The photograph is a close-up of the affected area:
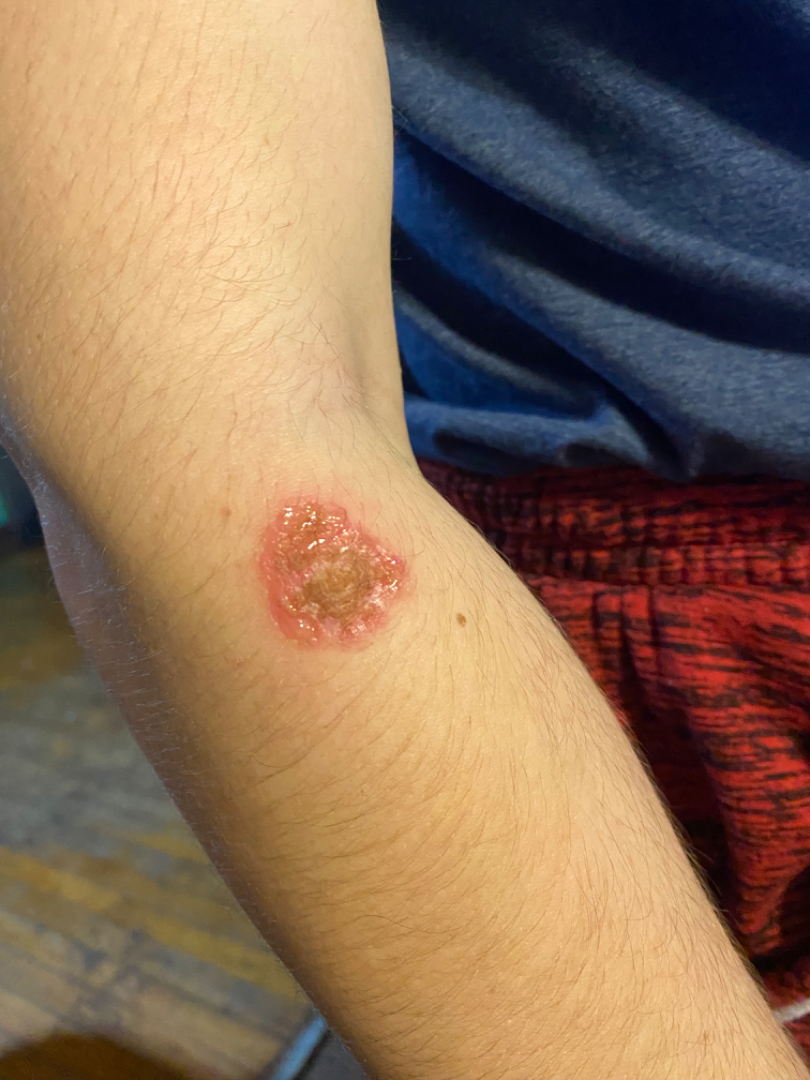differential = Deep fungal infection, Cutaneous leishmaniasis and Skin and soft tissue atypical mycobacterial infection were each considered, in no particular order.